Symptoms reported: itching and enlargement · a close-up photograph · the patient reported no systemic symptoms · the lesion is described as raised or bumpy · female contributor, age 18–29 · the affected area is the arm, back of the torso, leg and back of the hand · reported duration is more than five years · self-categorized by the patient as a rash — 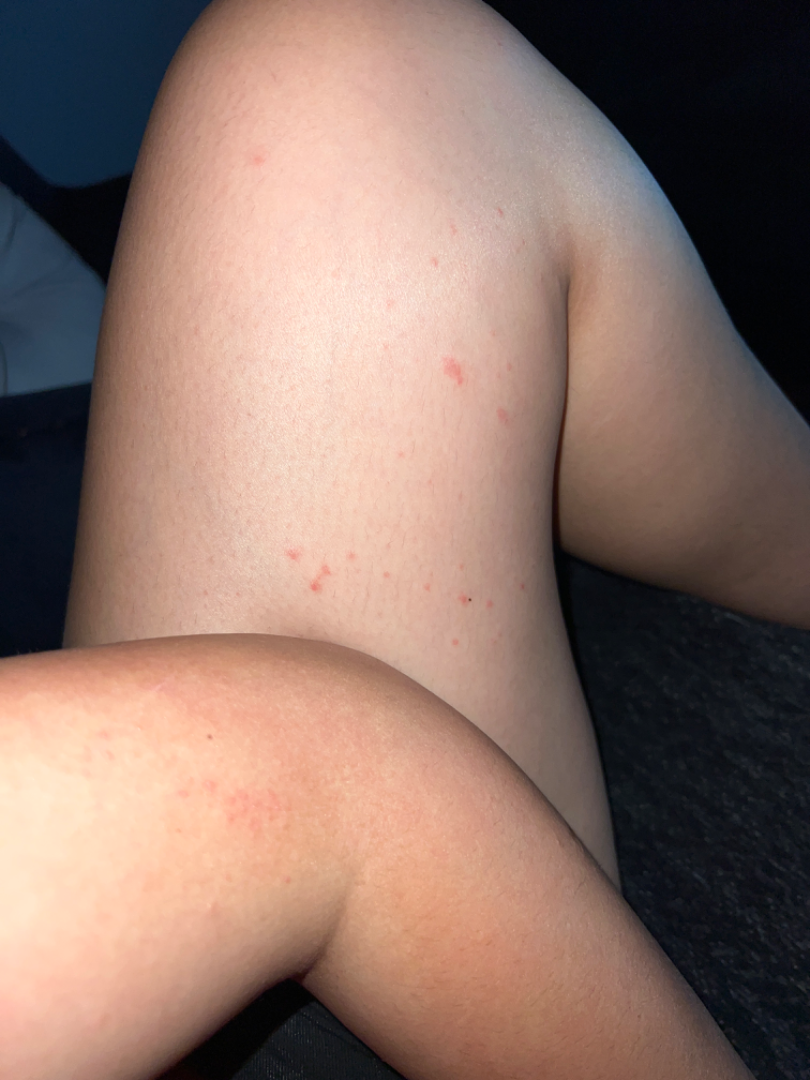On dermatologist assessment of the image: Folliculitis (leading); Urticaria (unlikely); Insect Bite (unlikely); Eczema (unlikely); Allergic Contact Dermatitis (unlikely).